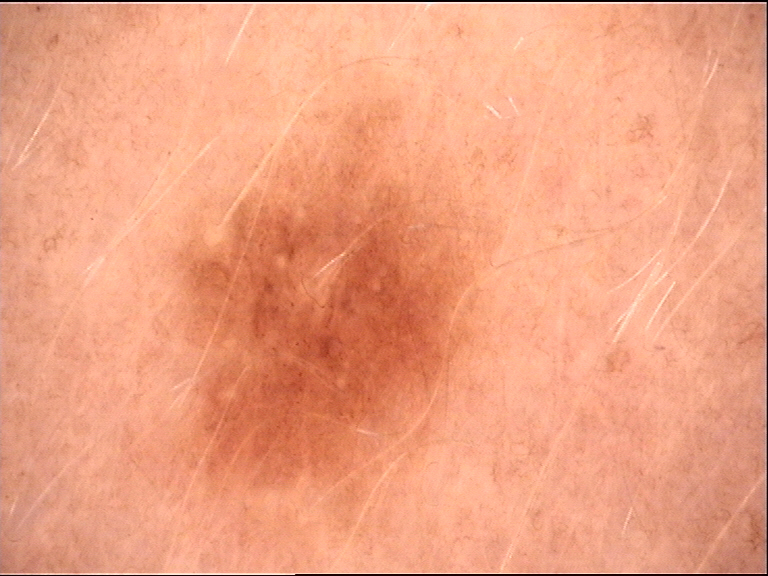image: dermatoscopy; lesion type: banal; assessment: junctional nevus (expert consensus).